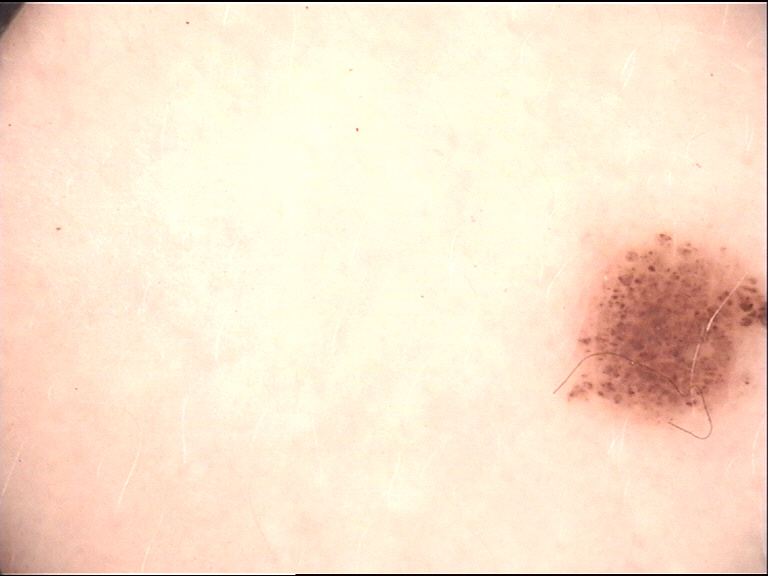Dermoscopy of a skin lesion.
The diagnosis was a dysplastic junctional nevus.